The leg, back of the hand, front of the torso and arm are involved. The contributor notes the condition has been present for less than one week. Self-categorized by the patient as a rash. The lesion is associated with itching, pain, enlargement and burning. The contributor is a female aged 50–59. The patient also reports joint pain and shortness of breath. A close-up photograph:
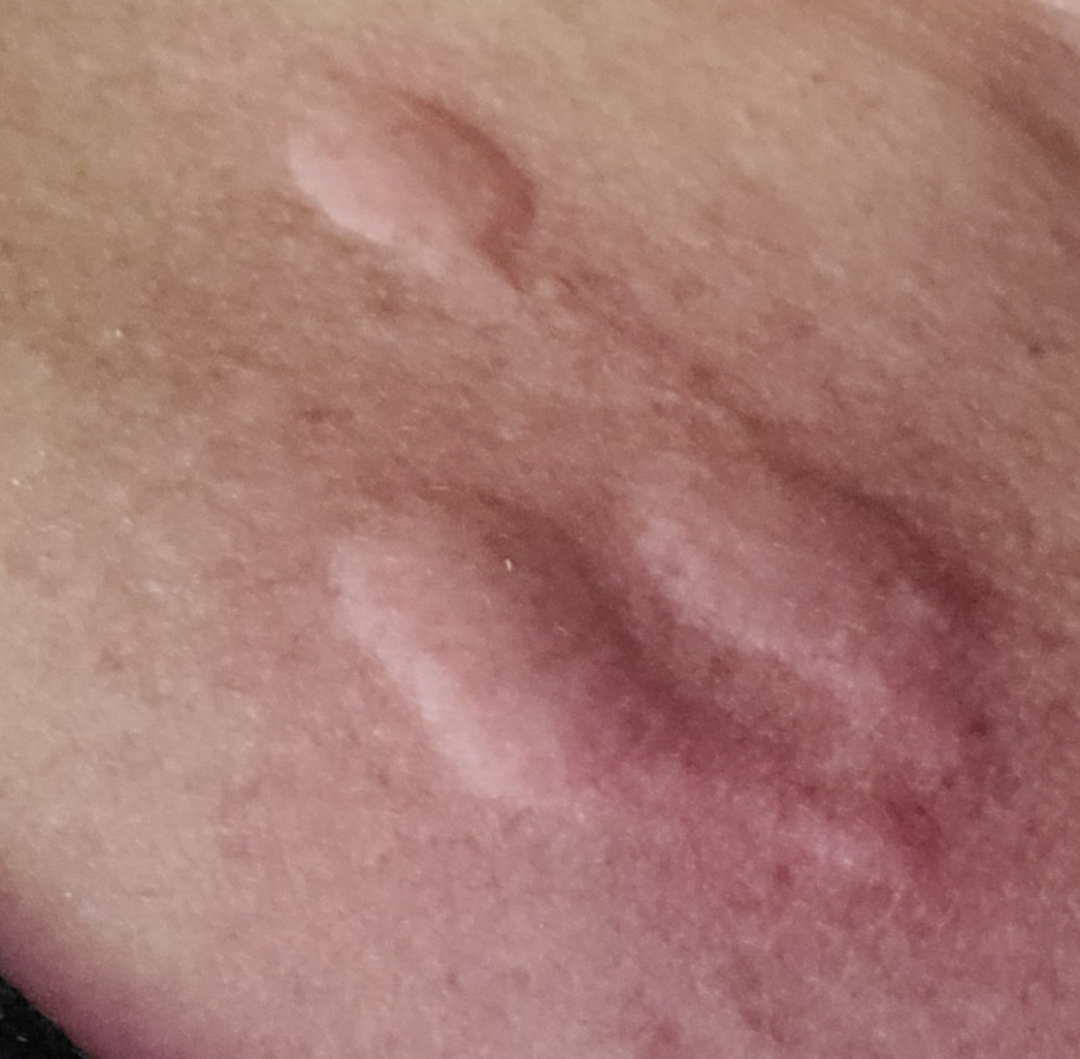Review: Reviewed remotely by one dermatologist: consistent with Urticaria.